A male subject about 75 years old · a contact-polarized dermoscopy image of a skin lesion.
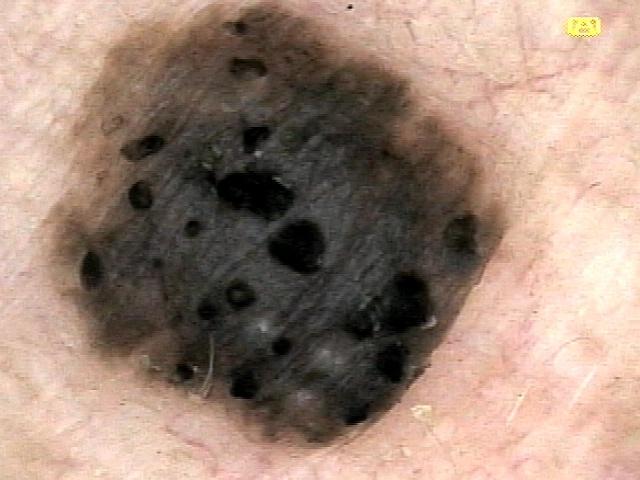The lesion is on the lateral trunk. Clinically diagnosed as a seborrheic keratosis.